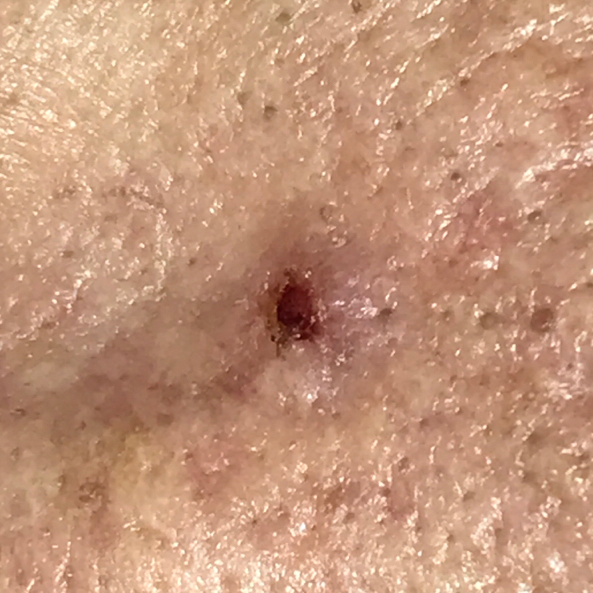Findings:
History notes pesticide exposure and prior malignancy (patient or family). Recorded as Fitzpatrick phototype III. A clinical photo of a skin lesion taken with a smartphone. The lesion is located on the nose. Measuring about 3 × 3 mm.
Conclusion:
On biopsy, the diagnosis was a basal cell carcinoma.